Present for one to four weeks. The contributor notes associated fatigue. The patient considered this a rash. The contributor notes the lesion is raised or bumpy. A close-up photograph. Fitzpatrick II; non-clinician graders estimated Monk Skin Tone 2 (US pool) or 3 (India pool). The lesion involves the arm. Symptoms reported: itching and enlargement:
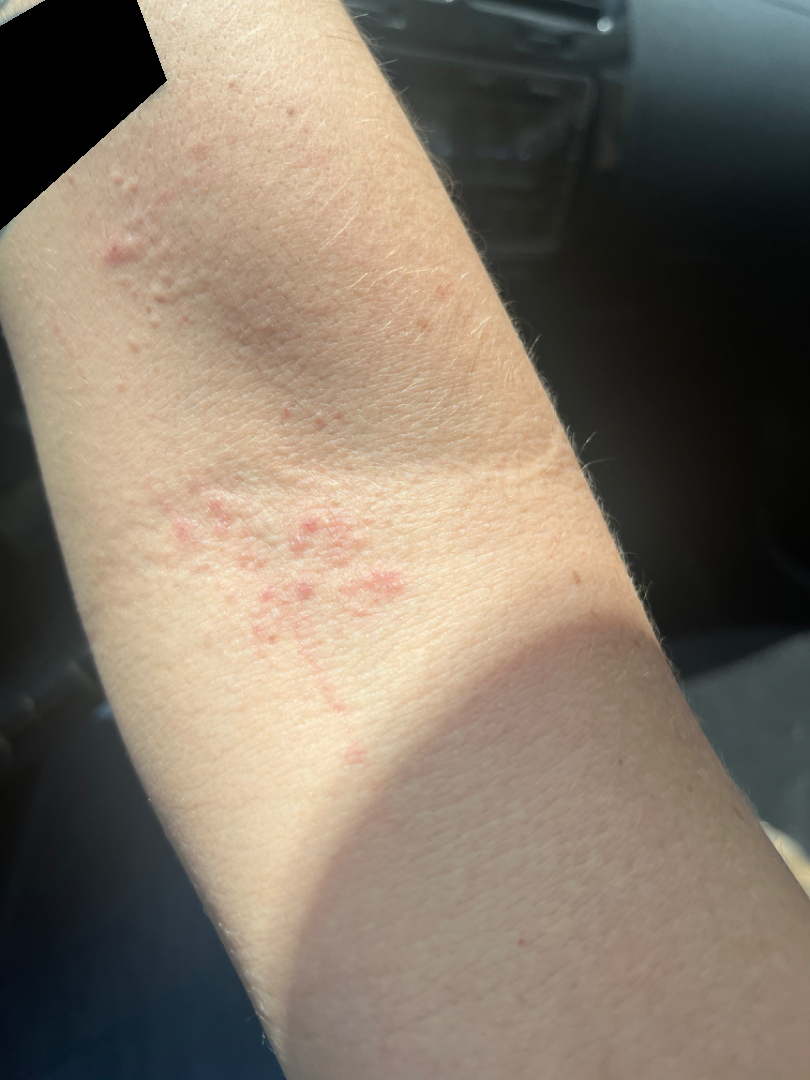On remote review of the image: Allergic Contact Dermatitis (55%); Eczema (27%); Urticaria (18%).